The contributor notes itching. Located on the front of the torso. Female patient, age 30–39. The contributor notes the condition has been present for about one day. The lesion is described as raised or bumpy. Skin tone: Fitzpatrick skin type III; human graders estimated MST 3. The patient considered this a rash. A close-up photograph: 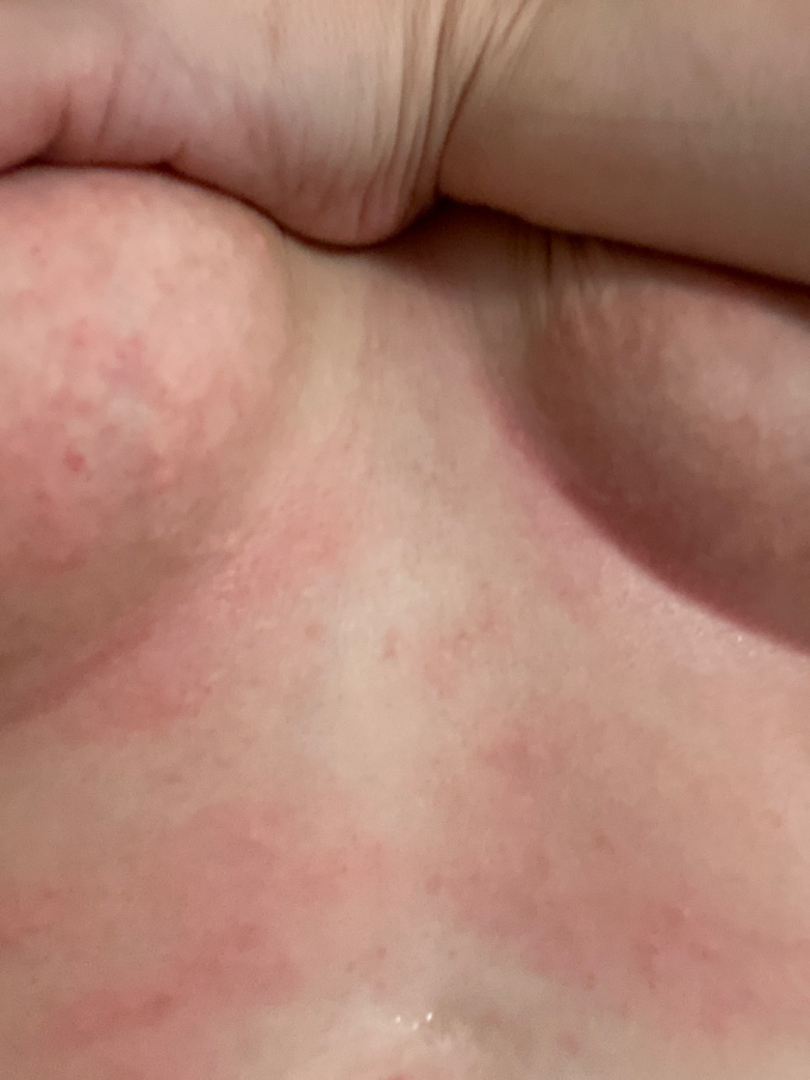Q: What was the assessment?
A: could not be assessed